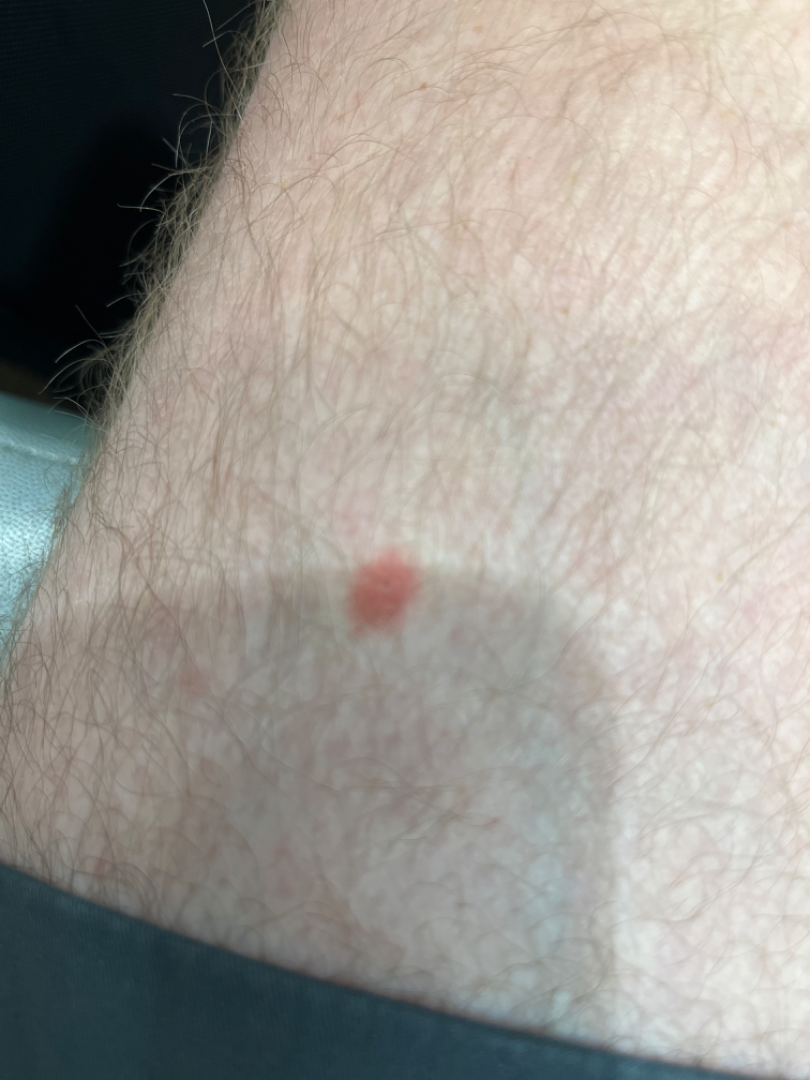assessment=could not be assessed
framing=close-up